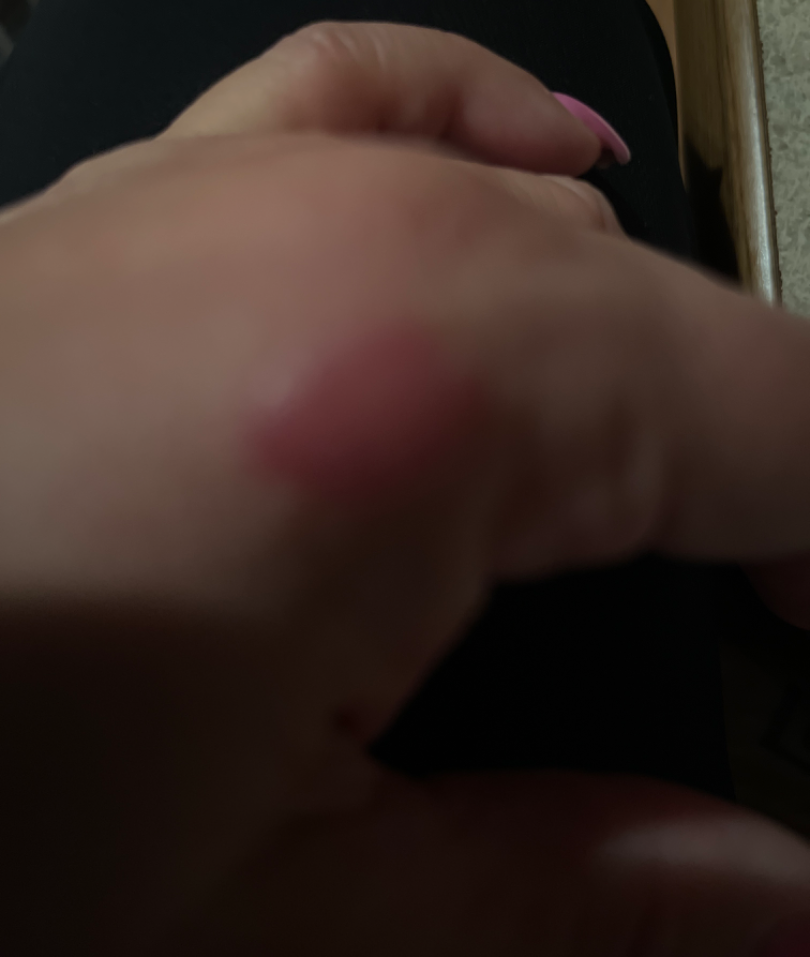Findings:
* assessment · could not be assessed
* location · back of the hand
* history · less than one week
* described texture · fluid-filled and raised or bumpy
* contributor · female, age 50–59
* self-categorized as · skin that appeared healthy to them
* framing · close-up
* skin tone · lay graders estimated MST 1 (US pool) or 2 (India pool)